A dermoscopy image of a single skin lesion:
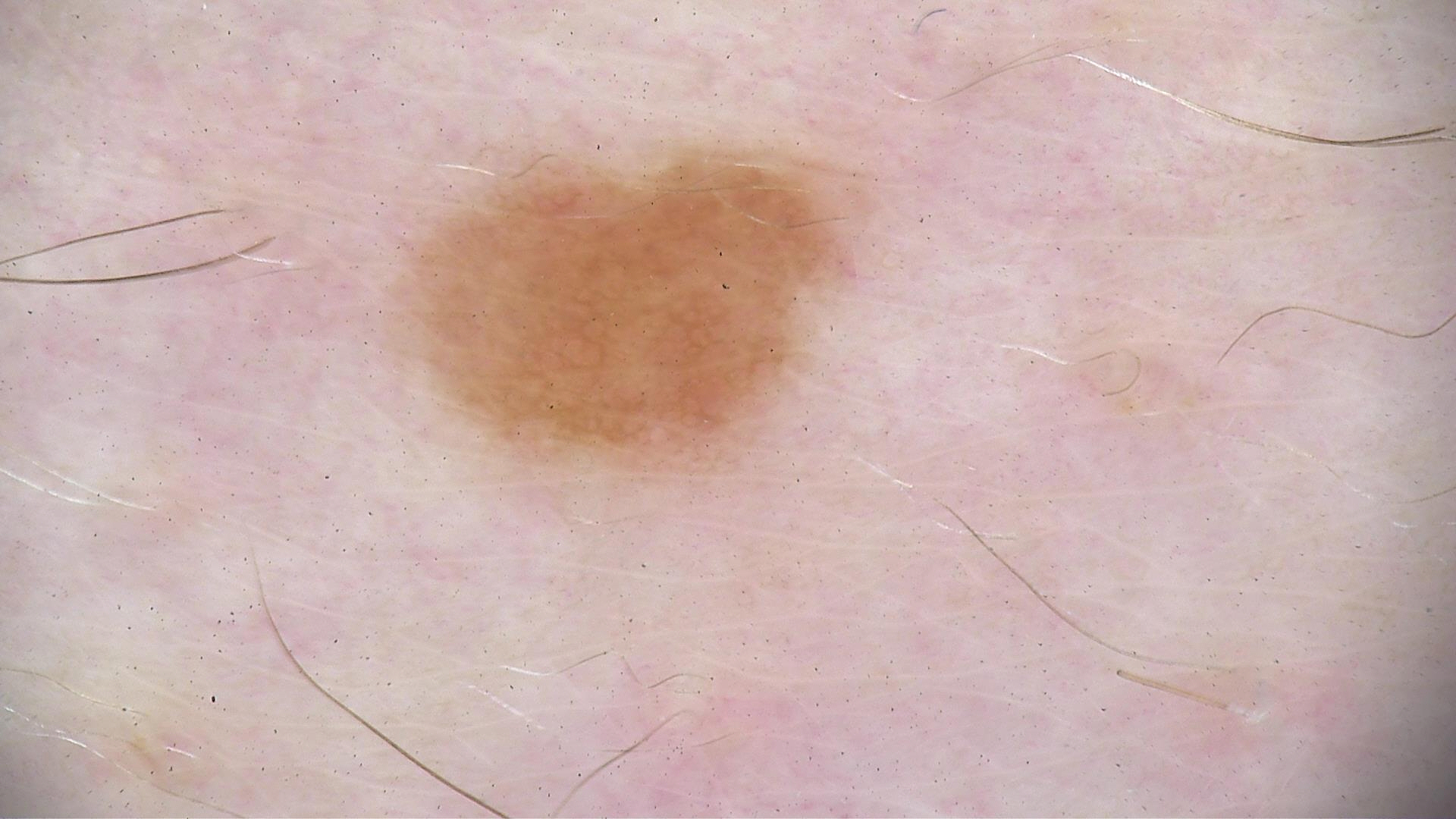The diagnostic label was a benign lesion — a dysplastic junctional nevus.